A contact-polarized dermoscopy image of a skin lesion. The chart notes melanoma in a first-degree relative. A male subject roughly 40 years of age. The patient was assessed as Fitzpatrick phototype III.
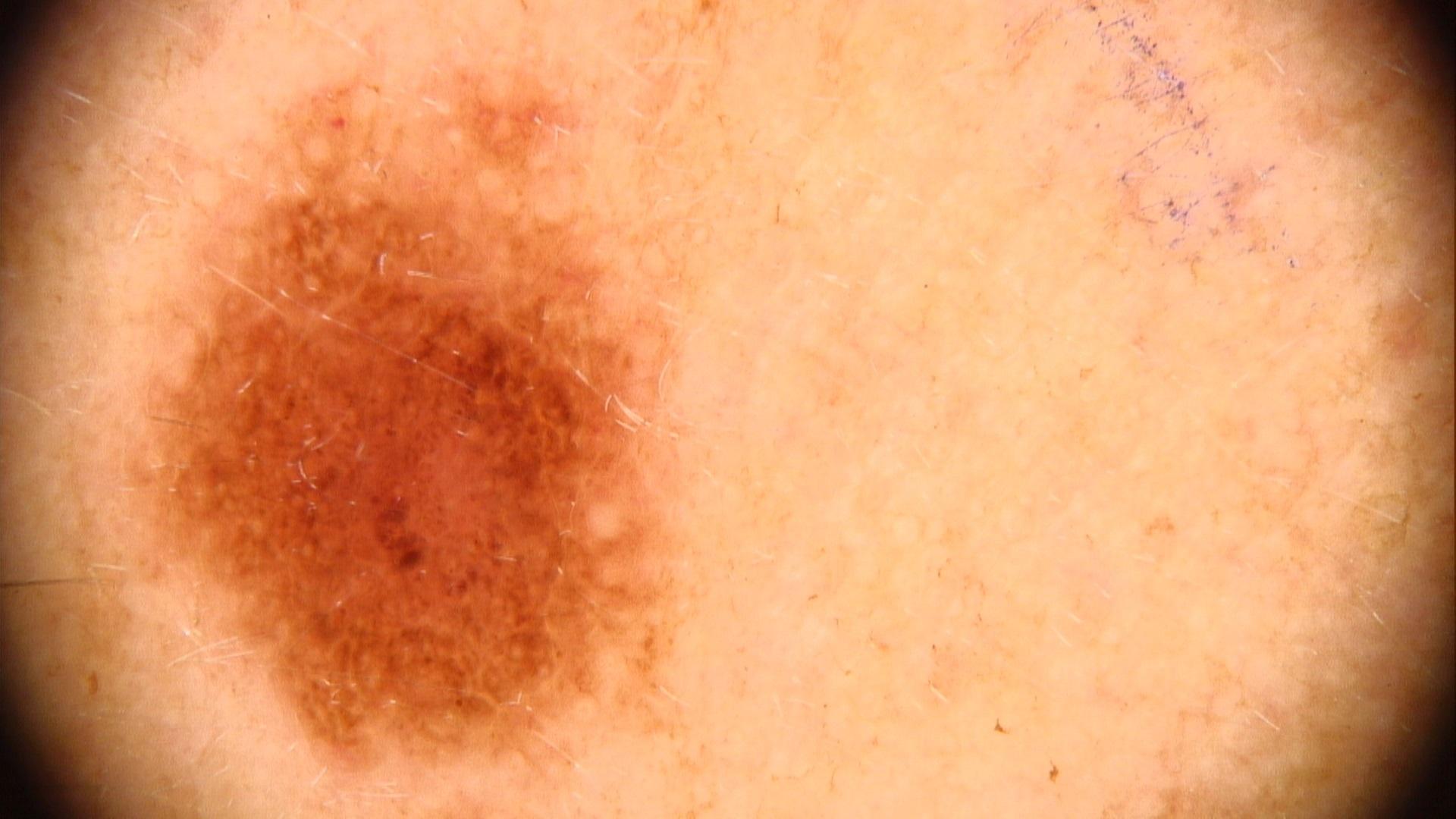The clinical impression was a benign, melanocytic lesion — a nevus.